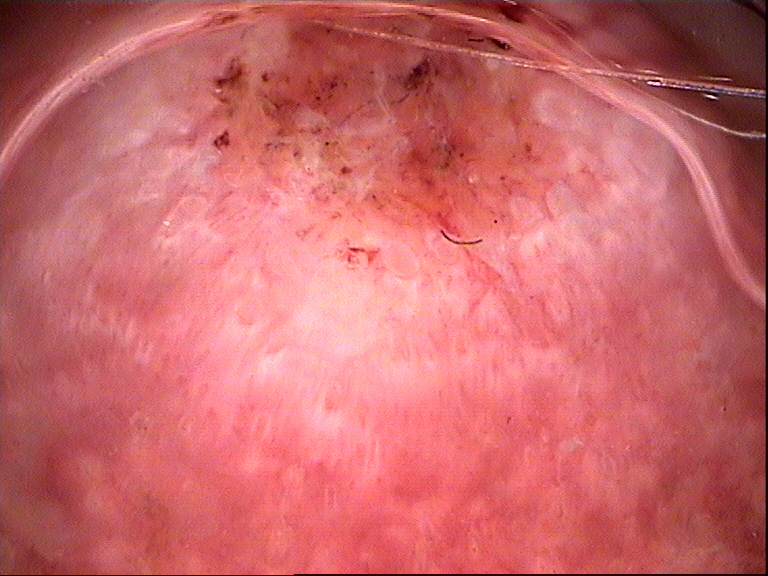A dermoscopy image of a single skin lesion.
Histopathologically confirmed as a keratinocytic lesion — a squamous cell carcinoma.